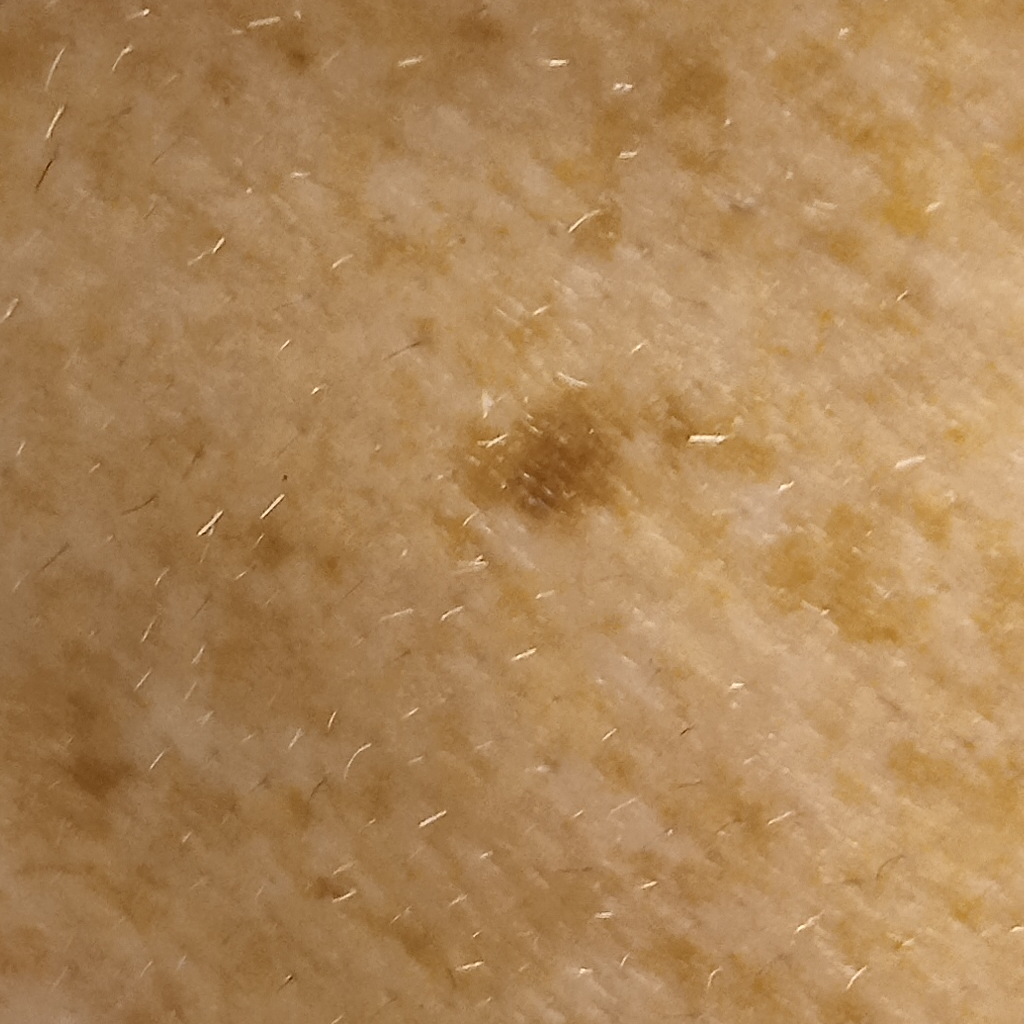The patient reports a personal history of cancer, no personal history of skin cancer, and no prior organ transplant. A clinical close-up of a skin lesion. Numerous moles by the patient's own estimate. The dermatologists' assessment was a melanoma.